A female patient, aged approximately 25. Dermoscopy of a skin lesion:
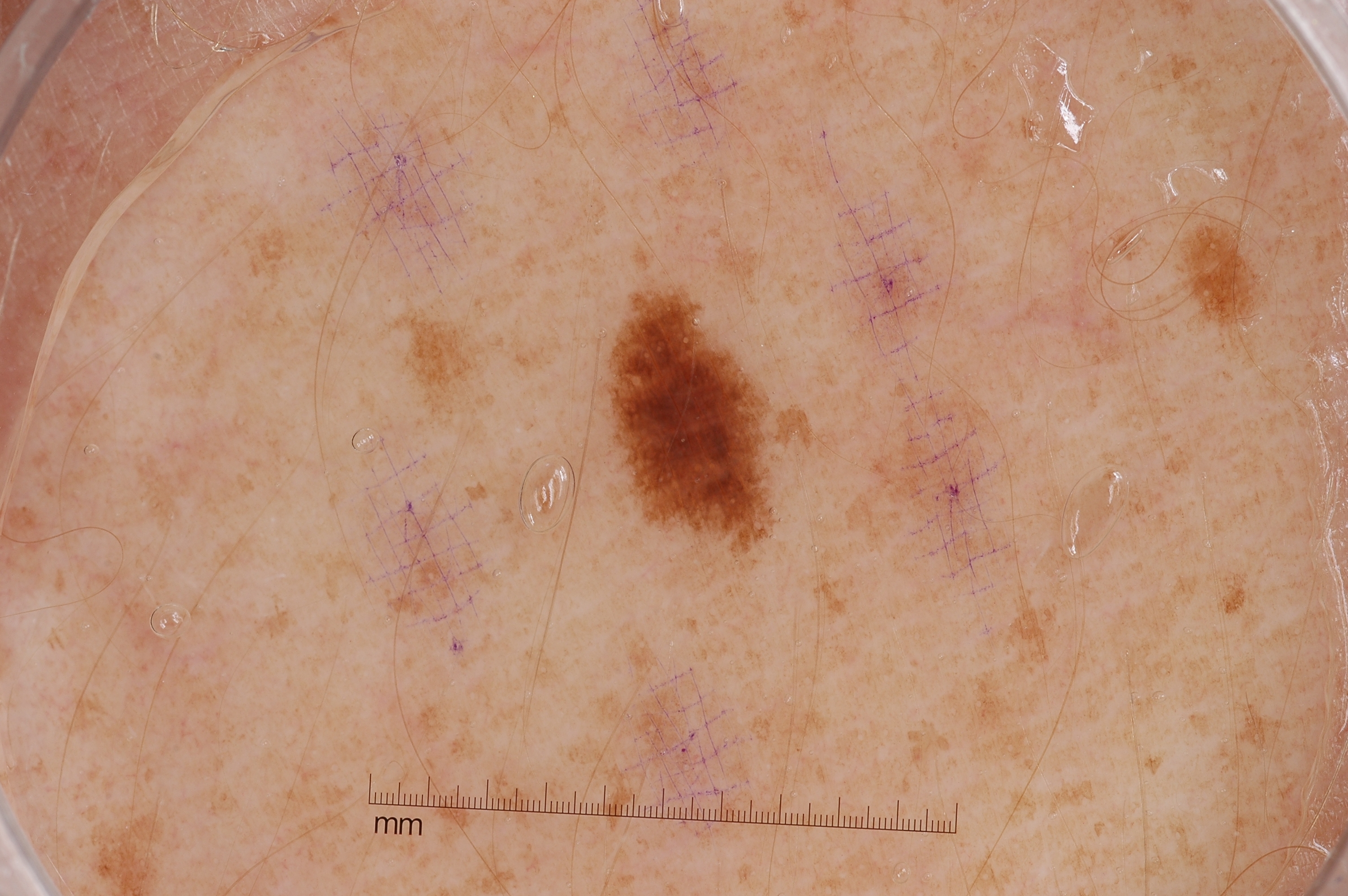dermoscopic findings = pigment network; absent: streaks, negative network, and milia-like cysts | lesion location = 603 289 776 553 | extent = small | diagnostic label = a melanocytic nevus.